Located on the leg; female patient, age 30–39; an image taken at a distance: 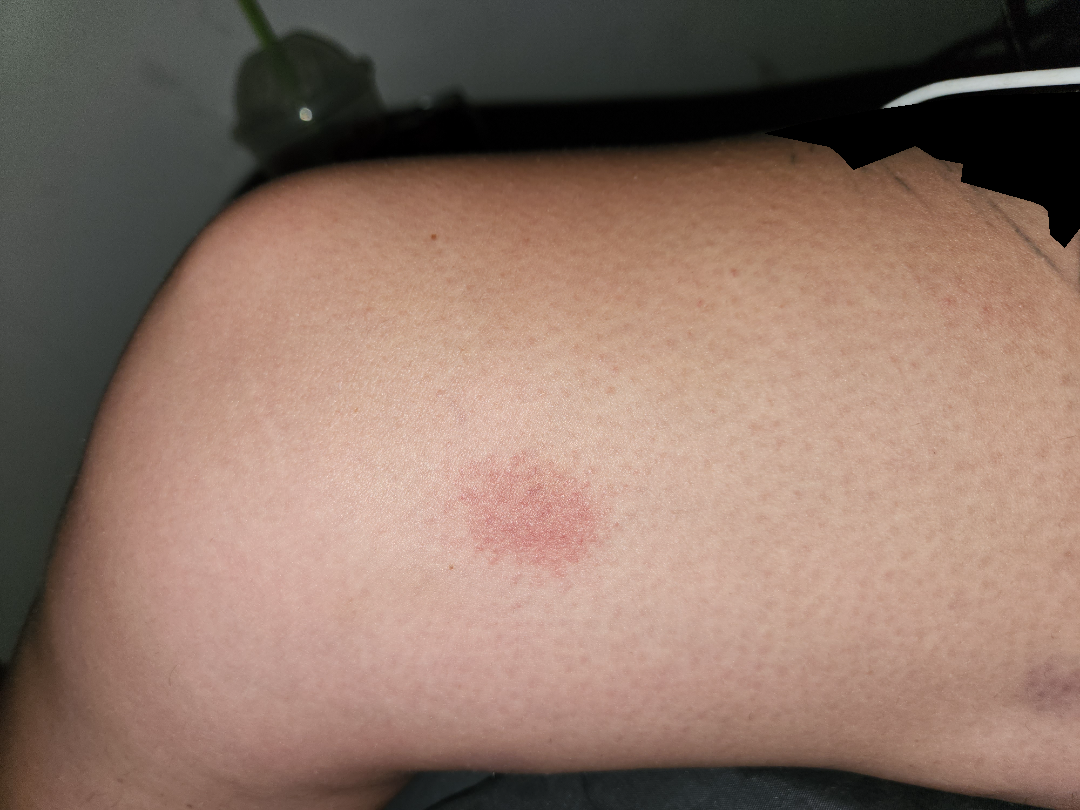Background:
The patient indicates enlargement, itching and bothersome appearance. The patient considered this a rash. Texture is reported as flat. Skin tone: Fitzpatrick IV. The patient indicates the condition has been present for less than one week.
Findings:
Pigmented purpuric eruption, Drug Rash and Eczema were each considered, in no particular order.